A clinical close-up photograph of a skin lesion:
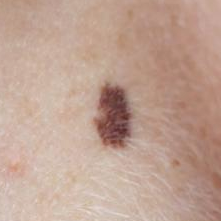Q: Where on the body is the lesion?
A: the face
Q: What symptoms does the patient report?
A: no change in appearance, no itching
Q: What did the workup show?
A: nevus (biopsy-proven)